A clinical photograph showing a skin lesion — 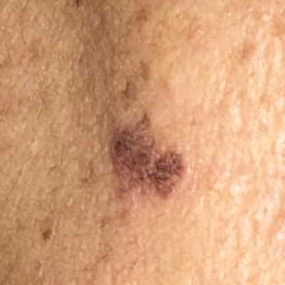Findings: The lesion was found on the face. Per patient report, the lesion is elevated, has grown, and itches, but has not bled. Conclusion: Clinically diagnosed as a seborrheic keratosis.